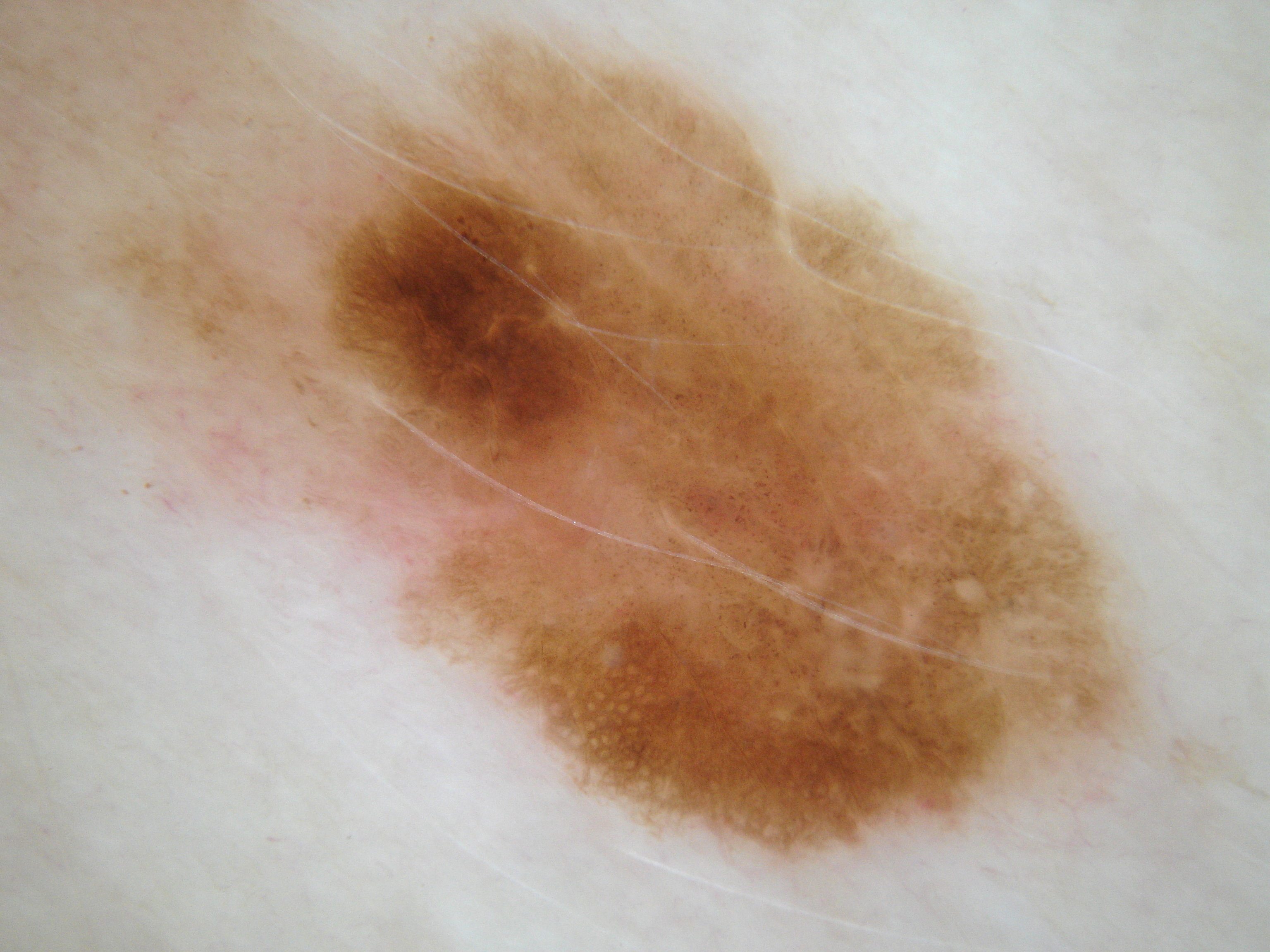Findings:
* imaging — dermoscopy
* dermoscopic findings — pigment network; absent: milia-like cysts, negative network, globules, and streaks
* lesion location — bbox(2, 1, 1161, 876)
* assessment — a melanocytic nevus, a benign lesion